The lesion involves the arm. The patient considered this a rash. The photograph is a close-up of the affected area. Texture is reported as rough or flaky and raised or bumpy:
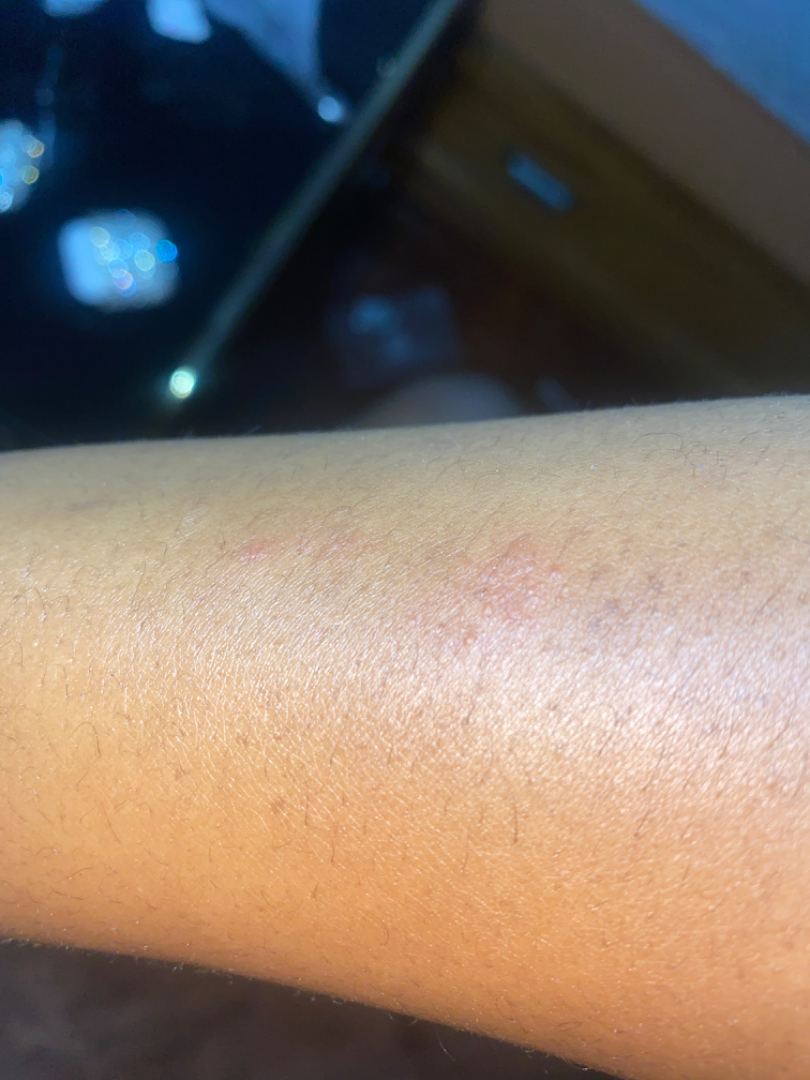| feature | finding |
|---|---|
| assessment | not assessable |